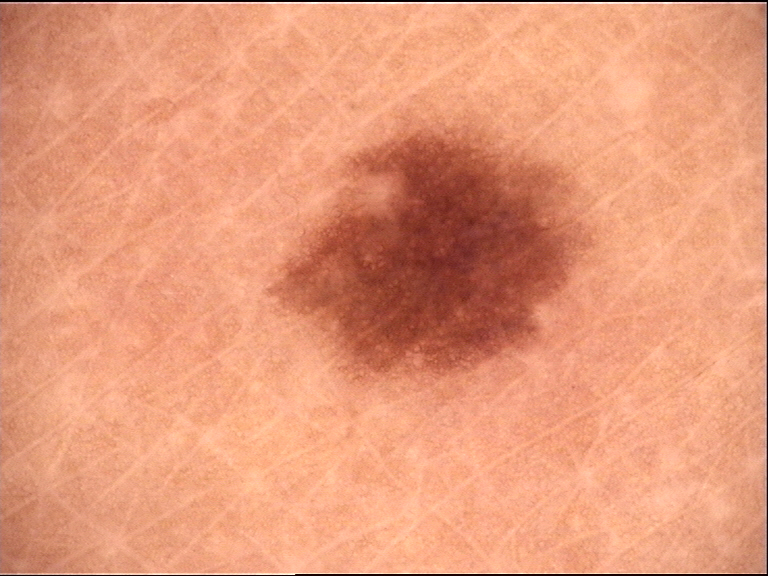Consistent with a junctional nevus.